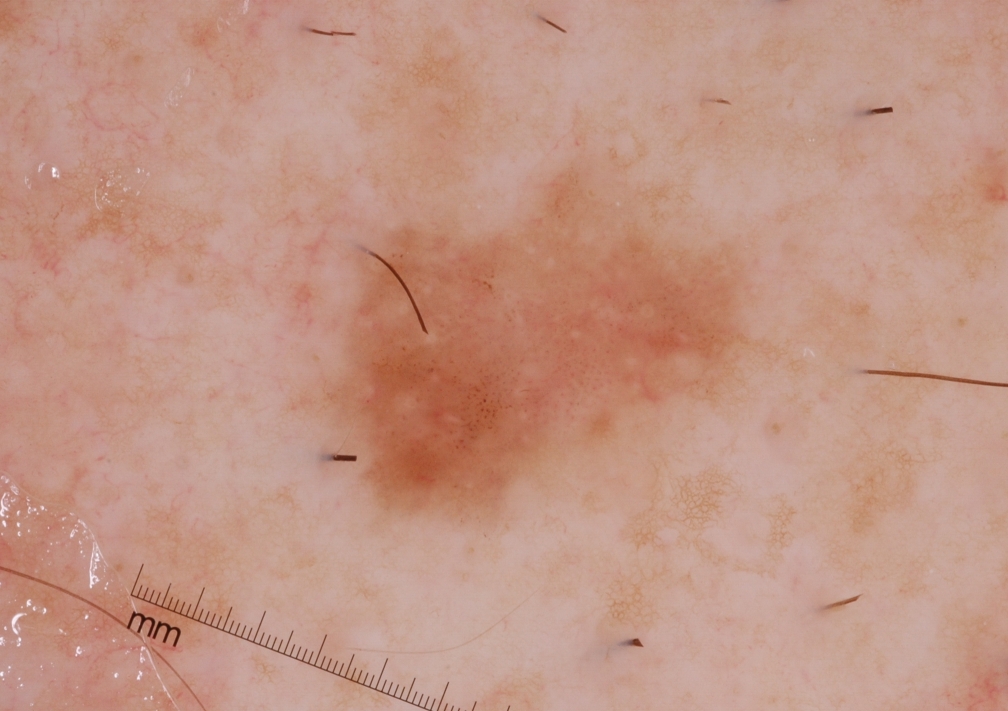A dermoscopic close-up of a skin lesion. Dermoscopically, the lesion shows globules; no pigment network, milia-like cysts, negative network, or streaks. As (left, top, right, bottom), the lesion's extent is bbox(301, 163, 751, 520). The lesion occupies roughly 13% of the field. Expert review diagnosed this as a melanocytic nevus.